This is a close-up image — 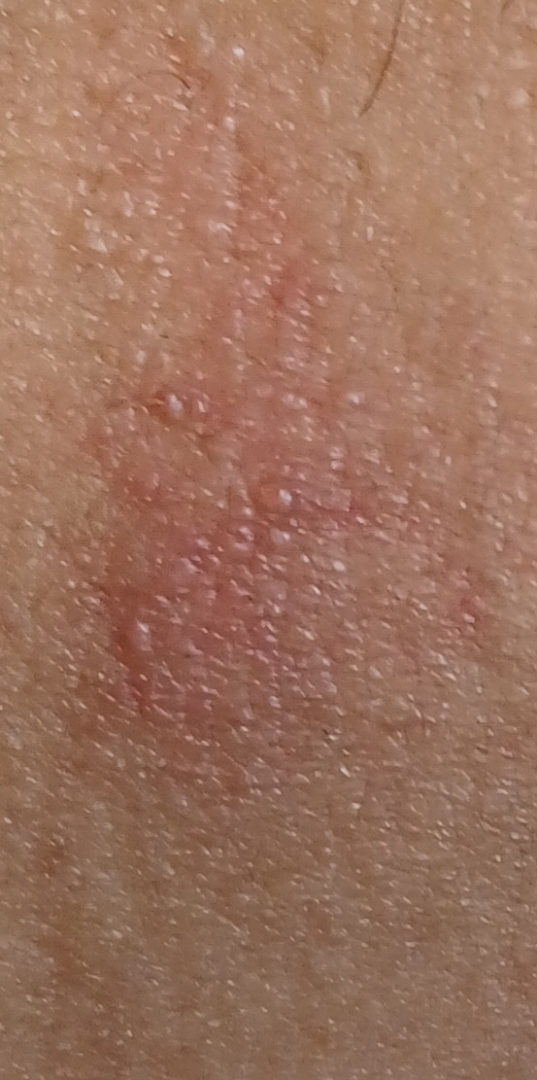Diagnostic features were not clearly distinguishable in this photograph.